A dermoscopic close-up of a skin lesion: 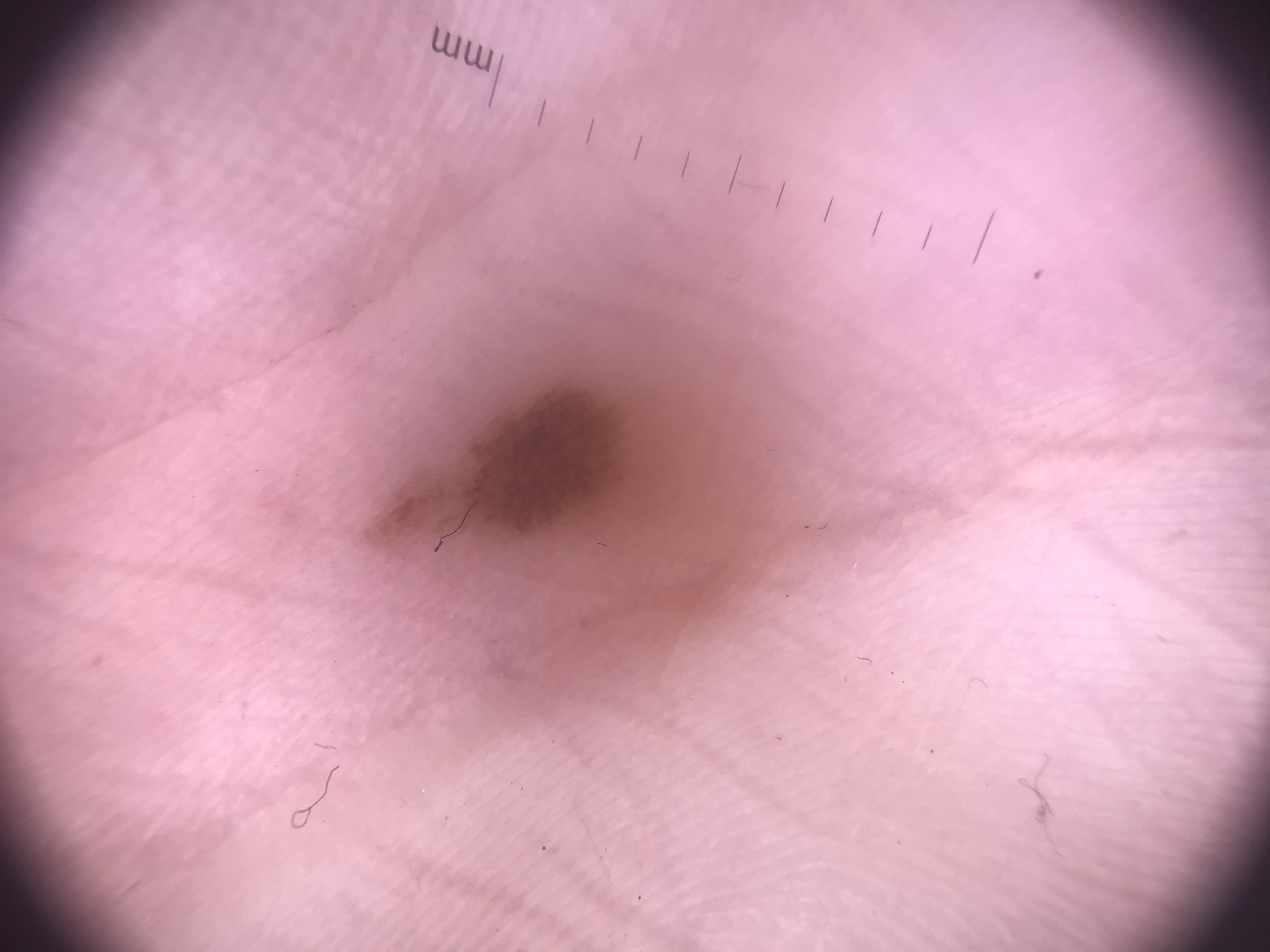Q: What kind of lesion is this?
A: banal
Q: What is this lesion?
A: acral junctional nevus (expert consensus)